A skin lesion imaged with a dermatoscope: 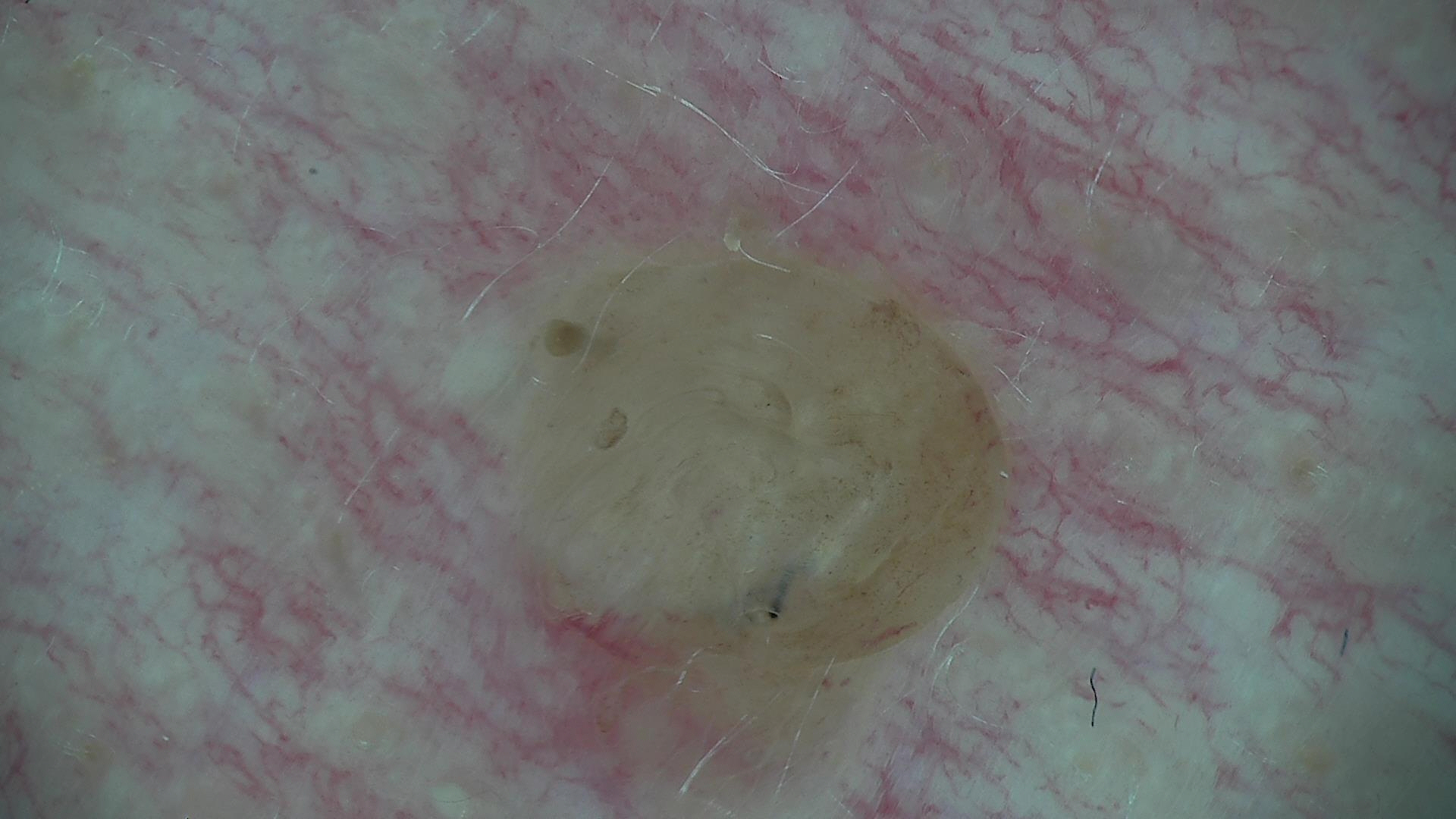Case:
* subtype · banal
* diagnosis · dermal nevus (expert consensus)